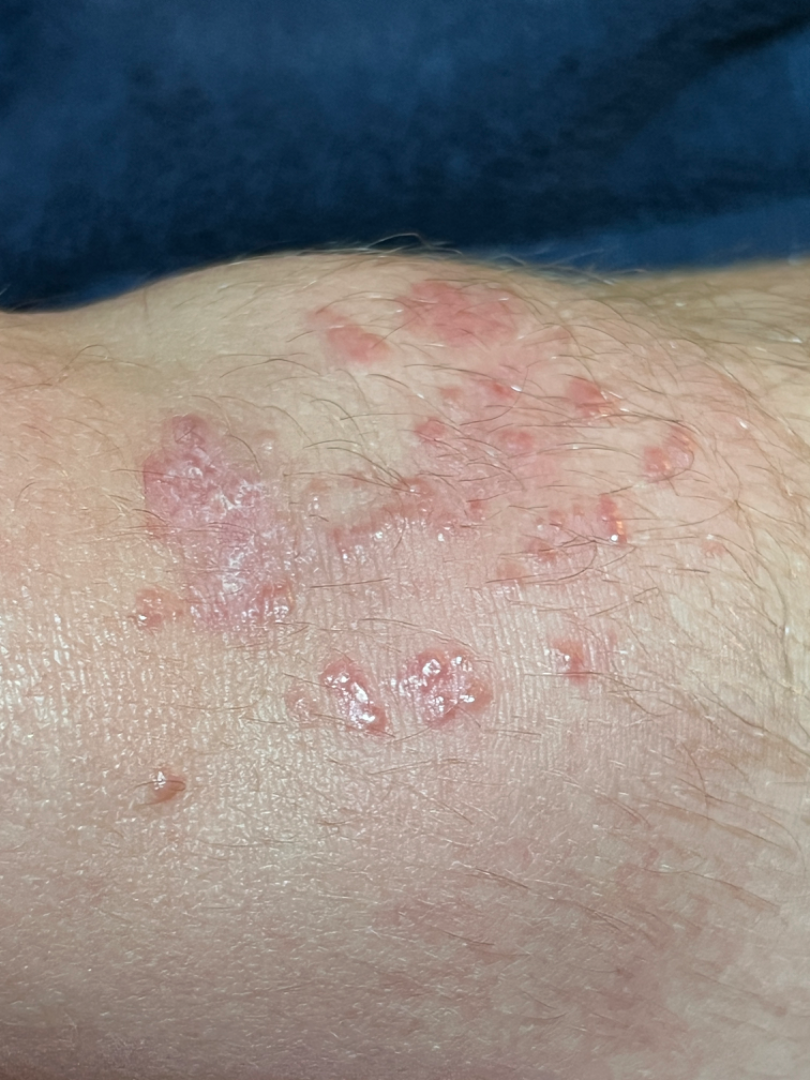The contributor reports the lesion is raised or bumpy. The leg is involved. The patient is a female aged 18–29. The photograph is a close-up of the affected area. The patient described the issue as a rash. The lesion is associated with itching. No constitutional symptoms were reported. Reported duration is one to four weeks. A single dermatologist reviewed the case: the leading consideration is Psoriasis; an alternative is Eczema.